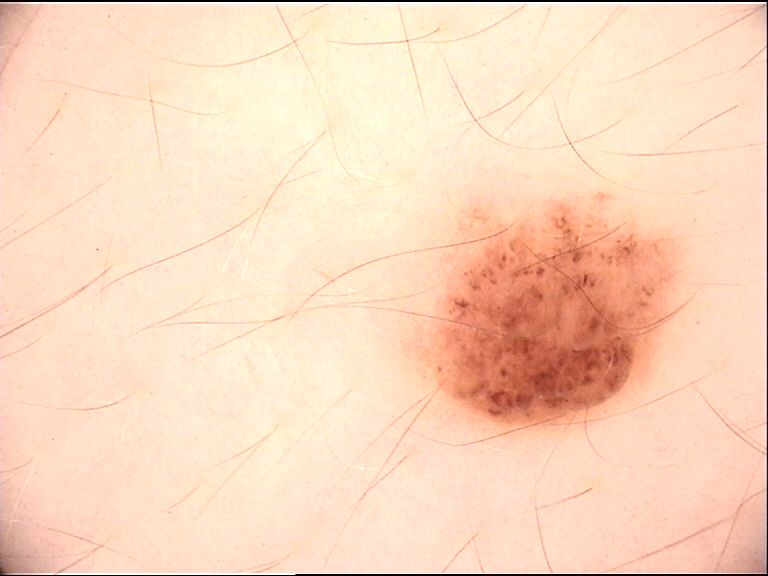| feature | finding |
|---|---|
| modality | dermatoscopy |
| class | dermal nevus (expert consensus) |